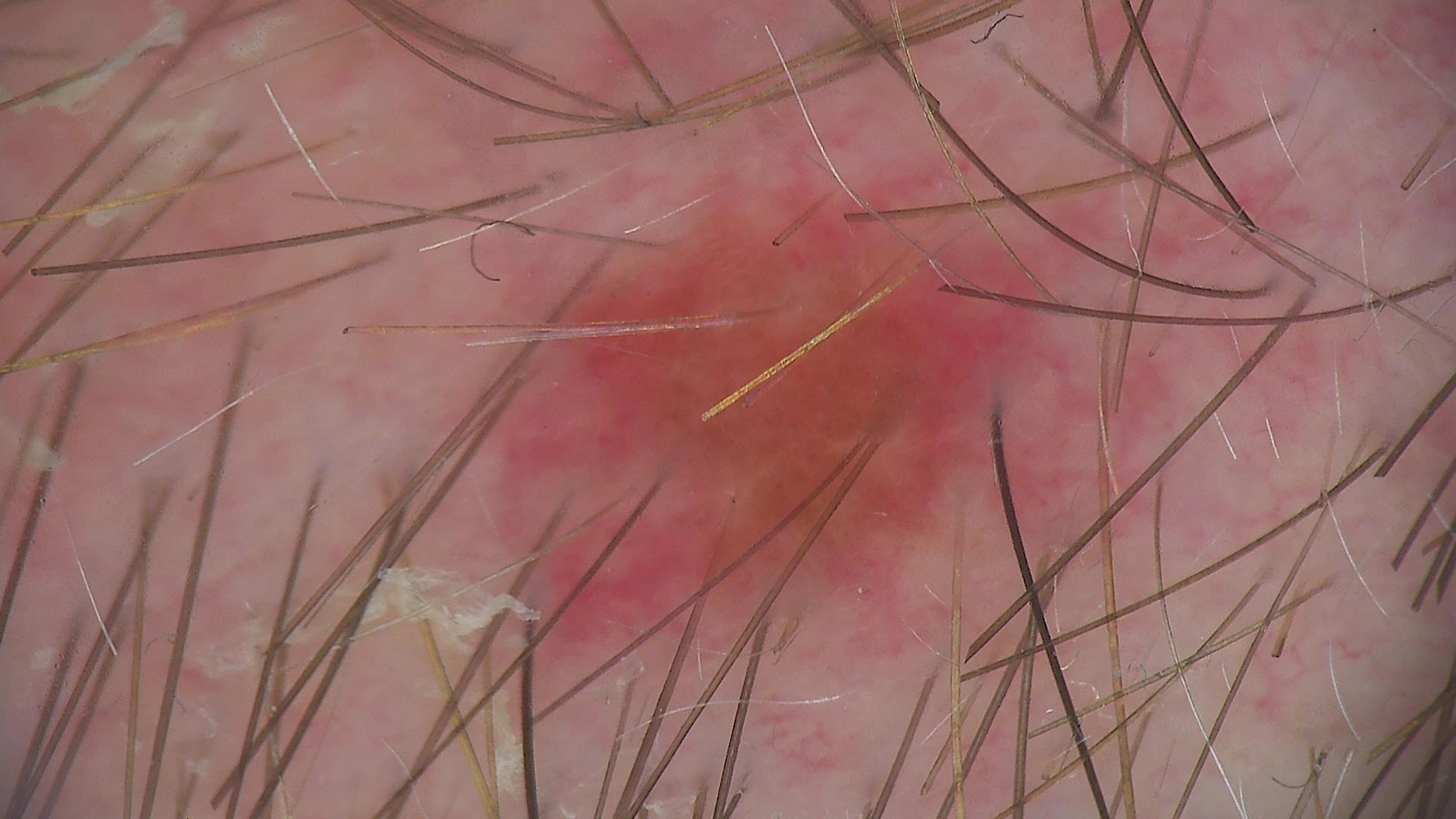A dermoscopic image of a skin lesion.
Consistent with a dysplastic junctional nevus.